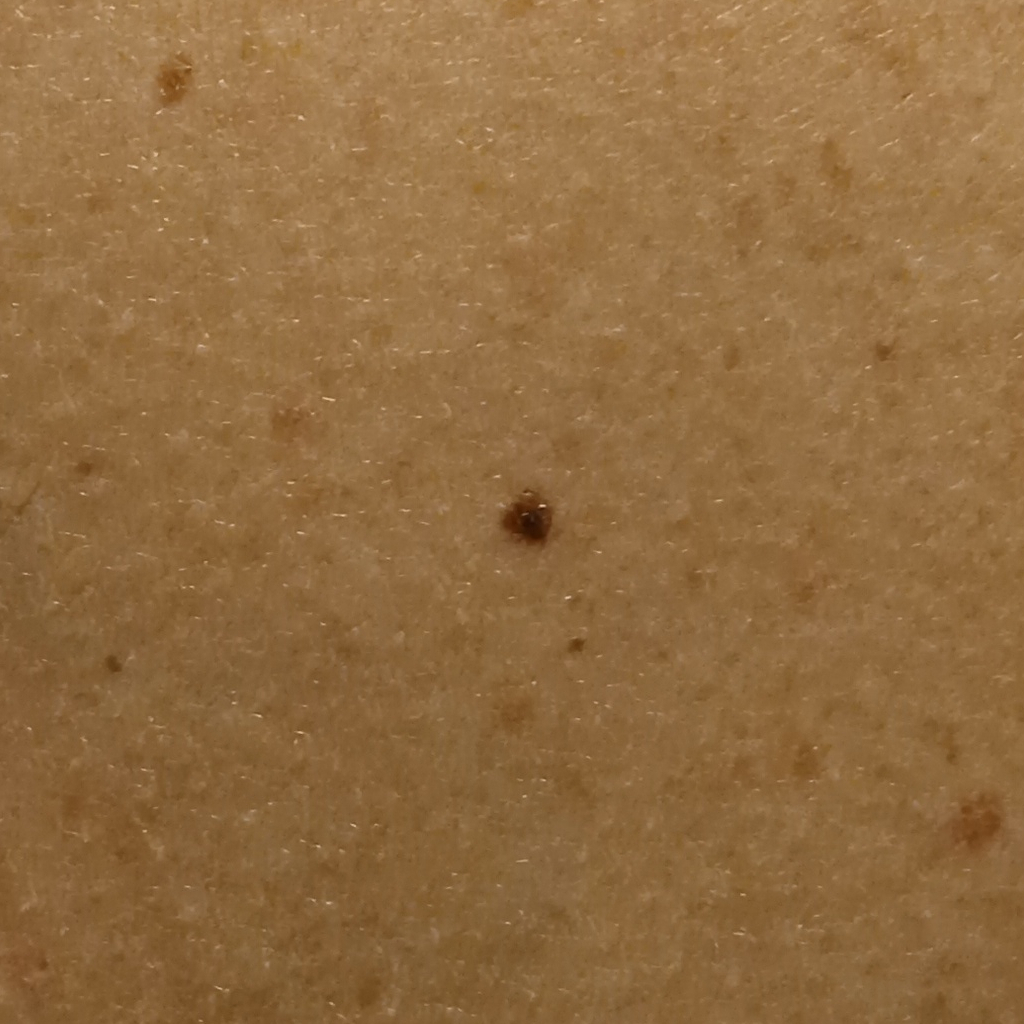The patient says their skin tans without first burning.
On a questionnaire the patient reported a family history of skin cancer, a personal history of cancer, and no prior organ transplant.
A female subject 64 years old.
A moderate number of moles by the patient's own estimate.
Referred for assessment of suspected seborrheic keratosis.
A clinical photograph of a skin lesion.
The lesion involves the back.
Measuring roughly 3.5 mm.
Histopathology confirmed a seborrheic keratosis, following excision.